An image taken at an angle. Self-categorized by the patient as skin that appeared healthy to them. The affected area is the head or neck, front of the torso and back of the torso. The condition has been present for three to twelve months. Skin tone: Fitzpatrick skin type III; lay reviewers estimated 3 on the MST. Reported lesion symptoms include itching. Male subject, age 18–29 — 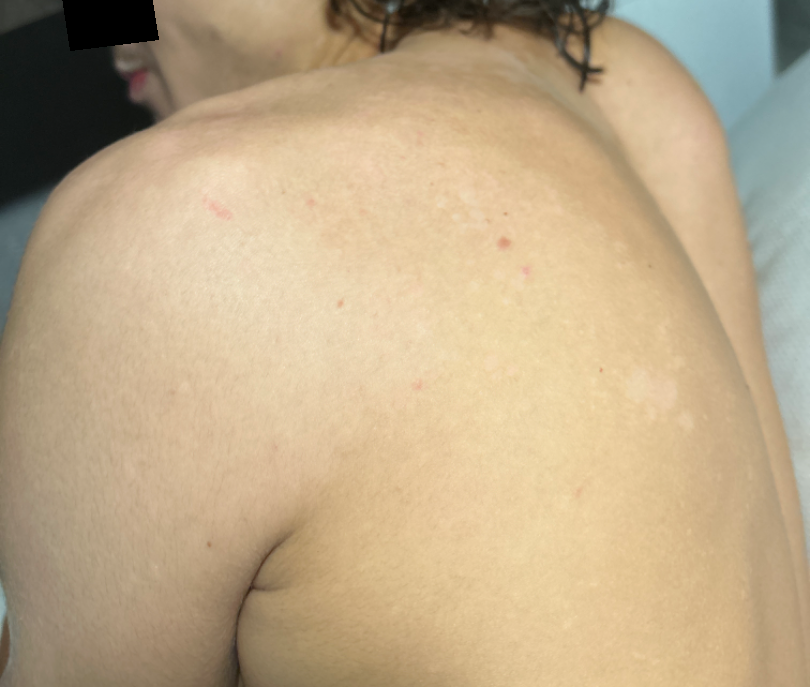On photographic review, the impression is Tinea Versicolor.